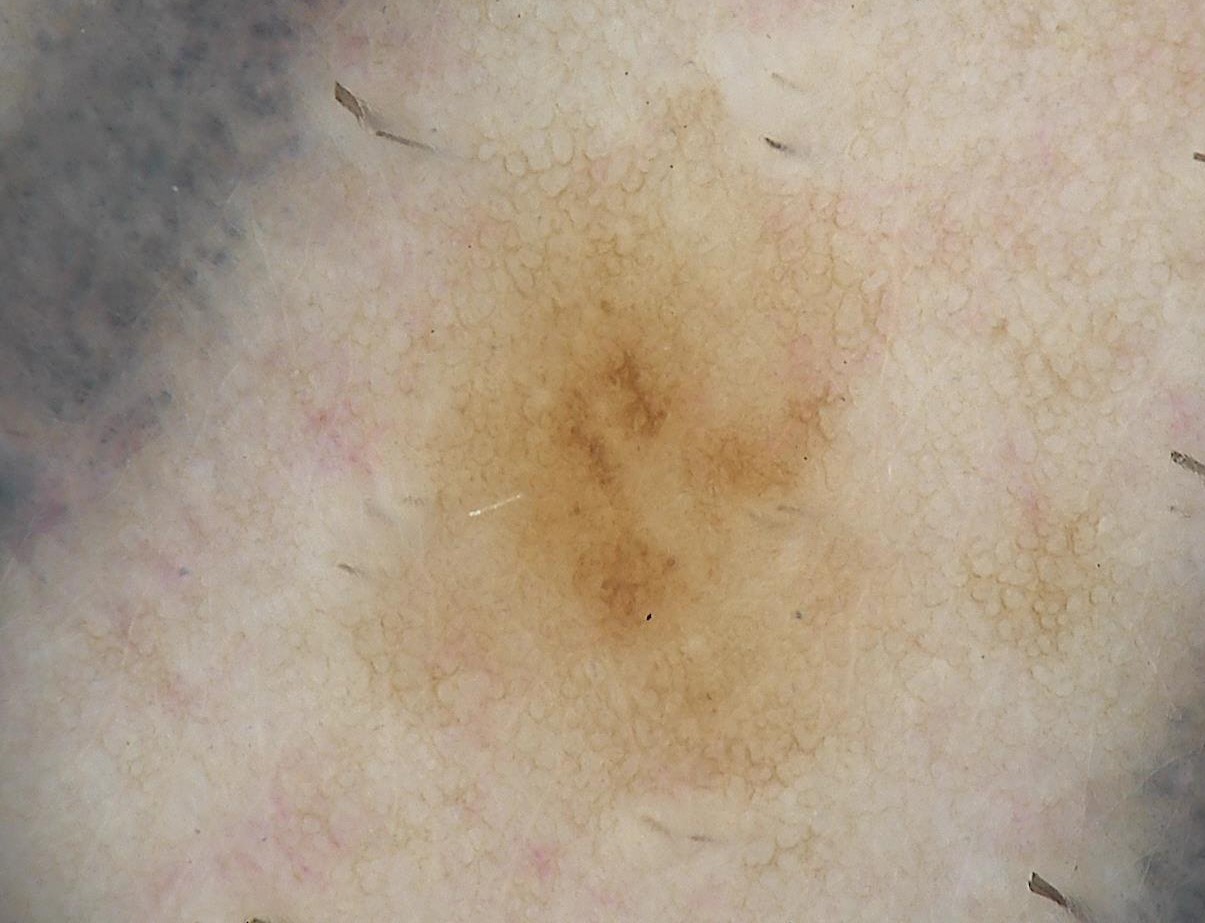The diagnostic label was a dysplastic junctional nevus.